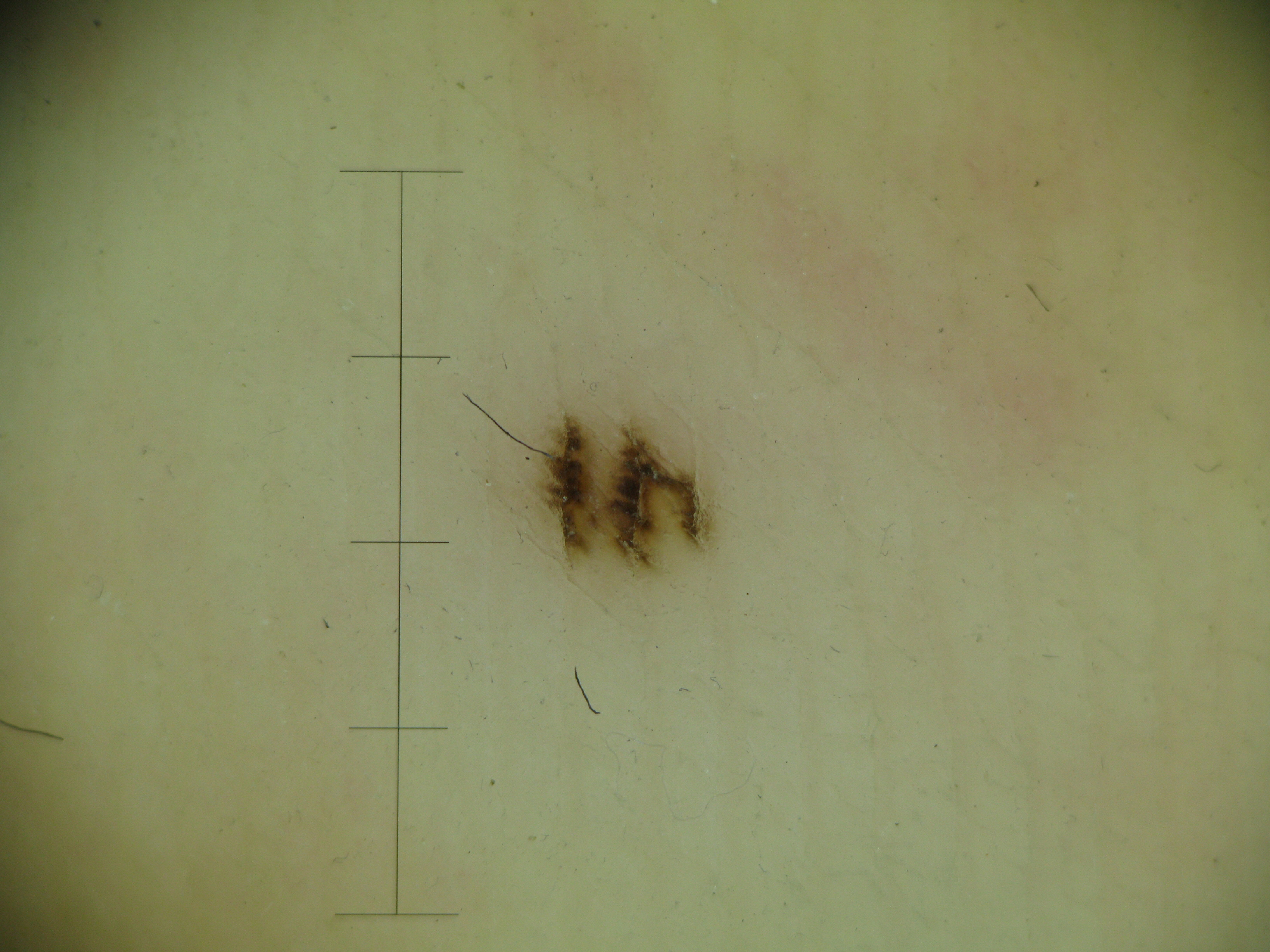Consistent with an acral junctional nevus.